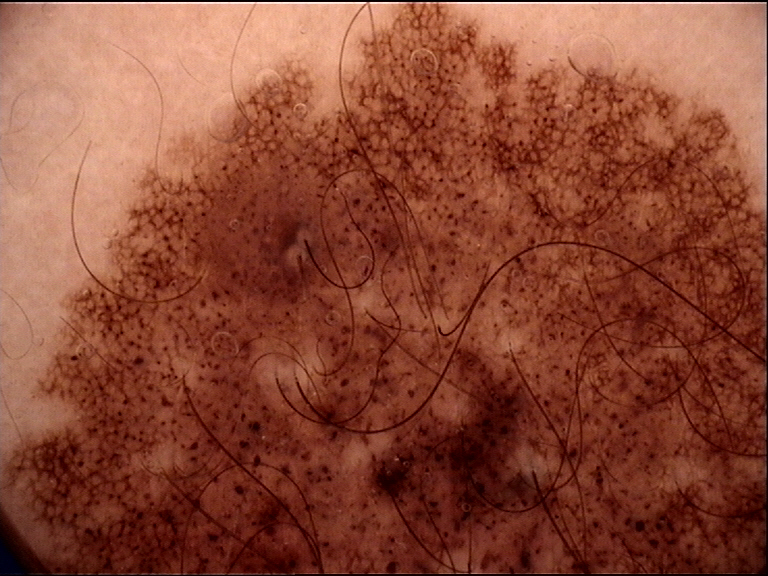A dermoscopy image of a single skin lesion.
Consistent with a banal lesion — a congenital compound nevus.